The patient indicates the lesion is rough or flaky and raised or bumpy; located on the front of the torso and head or neck; an image taken at a distance; the patient indicates pain, bothersome appearance, burning and itching; the patient described the issue as a rash:
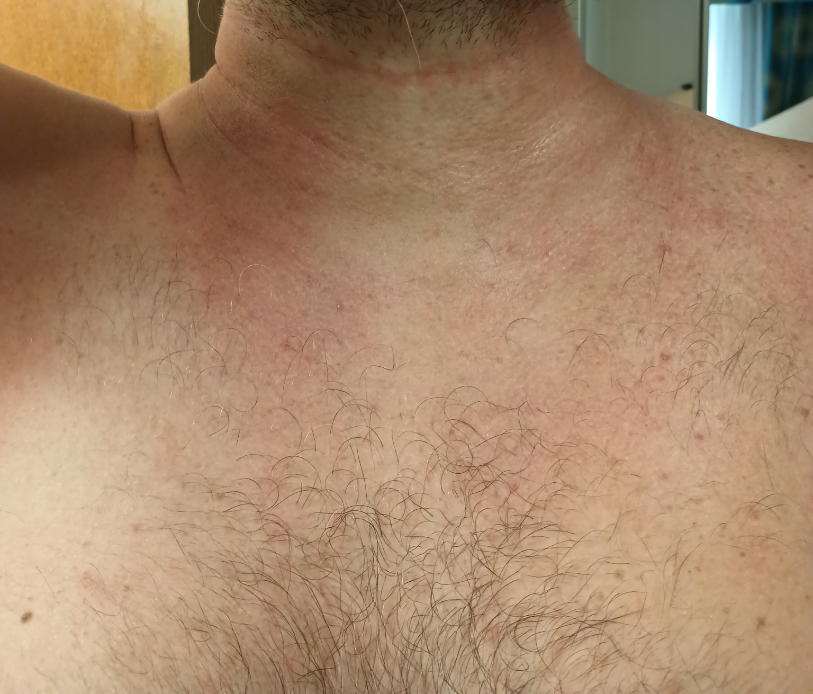A single dermatologist reviewed the case: the leading impression is Irritant Contact Dermatitis; also raised was Allergic Contact Dermatitis.